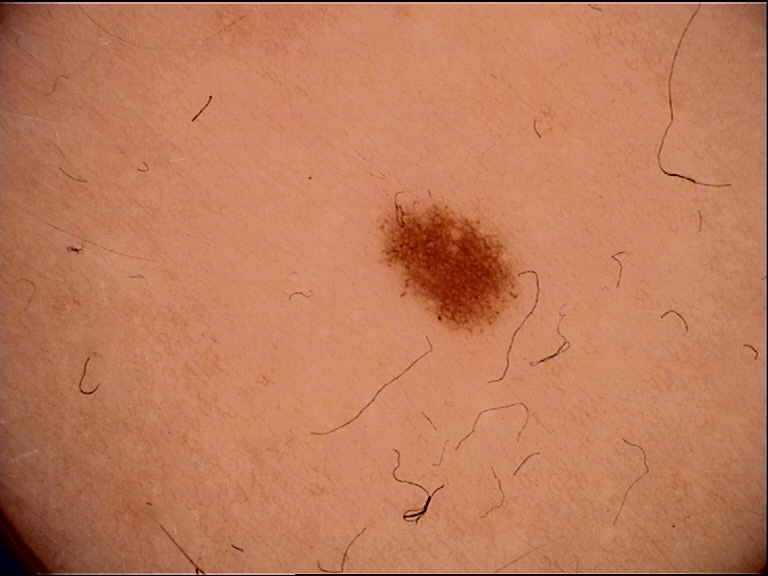A dermoscopic close-up of a skin lesion.
The diagnostic label was a benign lesion — a dysplastic junctional nevus.